A male subject, aged 48 to 52. A dermoscopic view of a skin lesion — 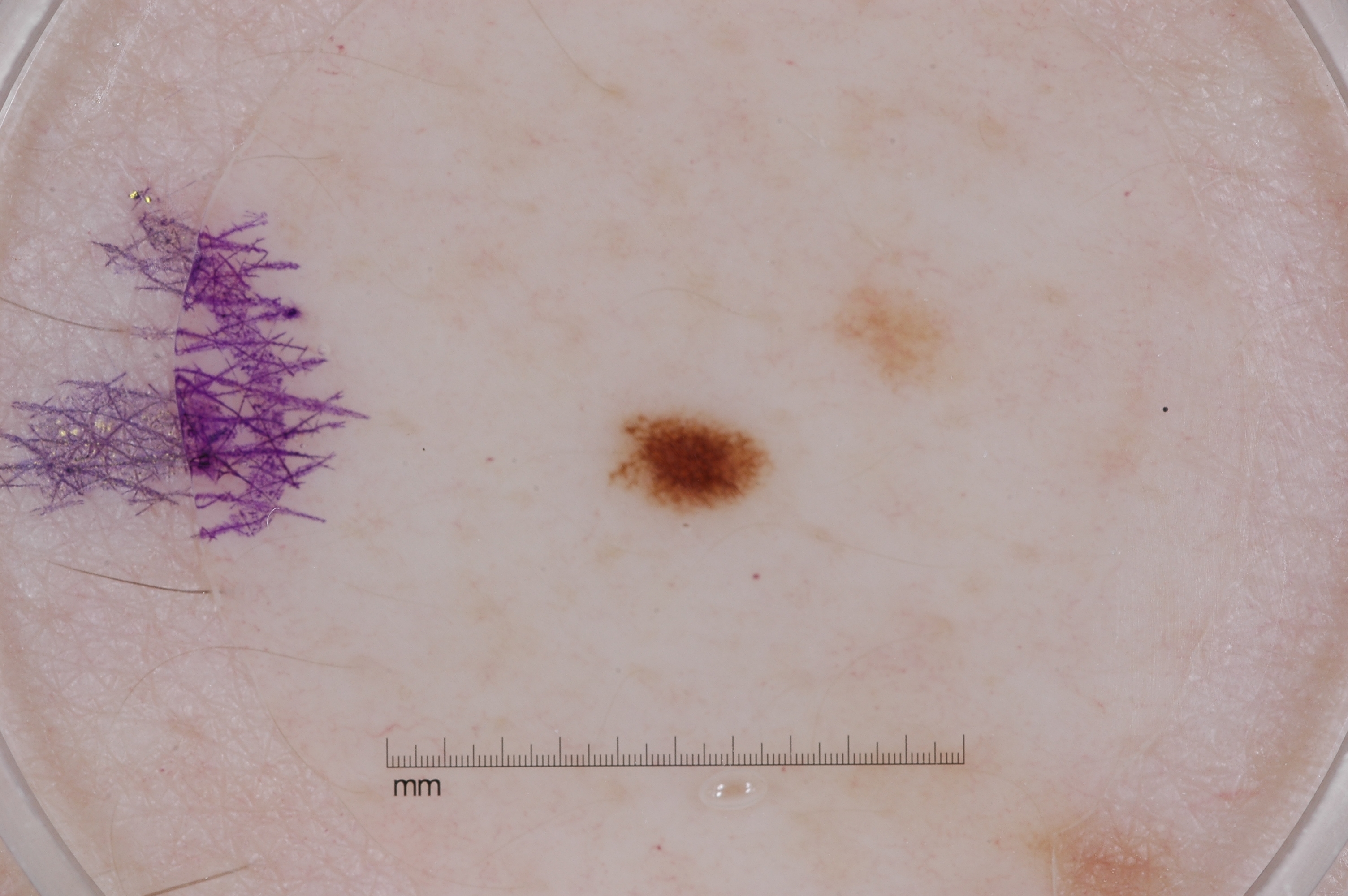{"lesion_extent": {"approx_field_fraction_pct": 1}, "lesion_location": {"bbox_xyxy": [606, 404, 778, 521]}, "dermoscopic_features": {"present": ["pigment network"], "absent": ["streaks", "milia-like cysts", "negative network"]}, "diagnosis": {"name": "melanocytic nevus", "malignancy": "benign", "lineage": "melanocytic", "provenance": "clinical"}}